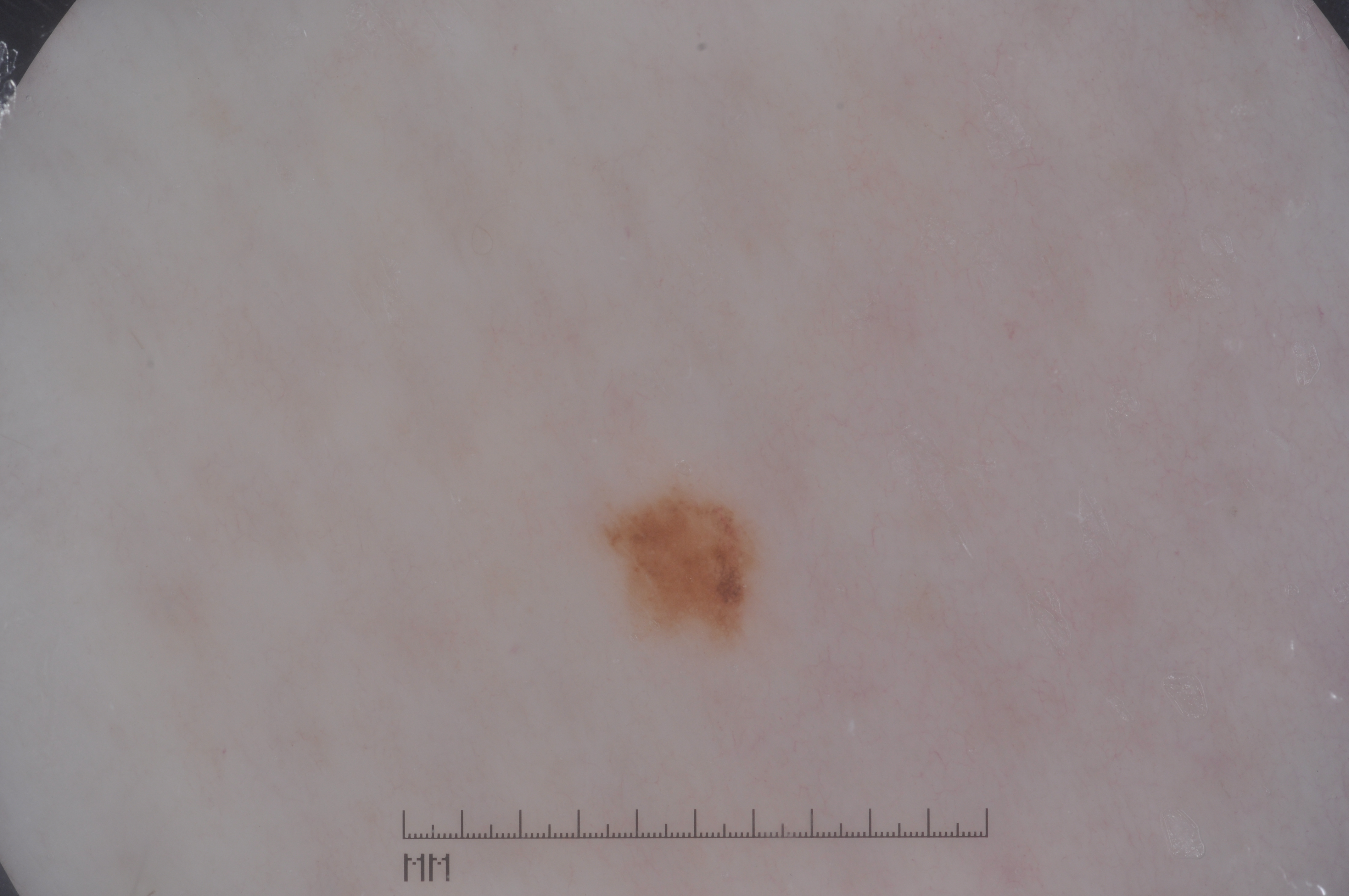Summary: Dermoscopy of a skin lesion. Dermoscopic examination shows pigment network, with no streaks, negative network, or milia-like cysts. Lesion location: bbox=[588, 474, 767, 657]. Conclusion: Clinically diagnosed as a melanocytic nevus.